The lesion is described as raised or bumpy · the patient considered this a rash · an image taken at a distance · symptoms reported: itching · female subject, age 18–29 · the affected area is the arm · skin tone: Fitzpatrick skin type III; lay reviewers estimated MST 1–2 — 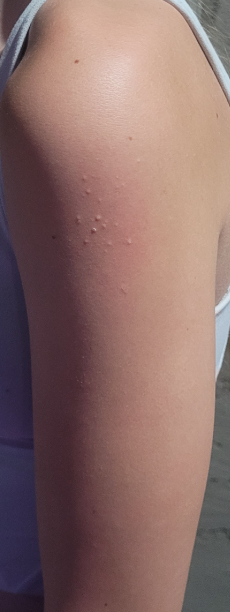  assessment: not assessable